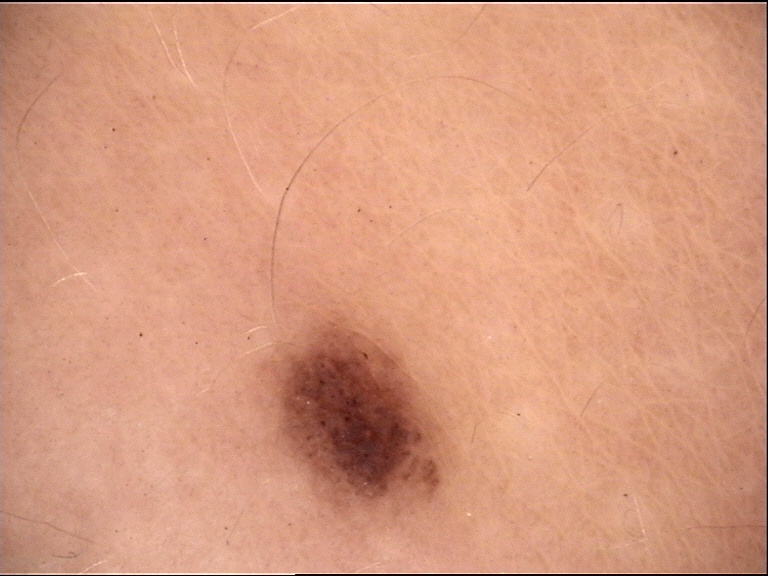Case:
A dermatoscopic image of a skin lesion. The architecture is that of a banal lesion.
Conclusion:
Labeled as a compound nevus.